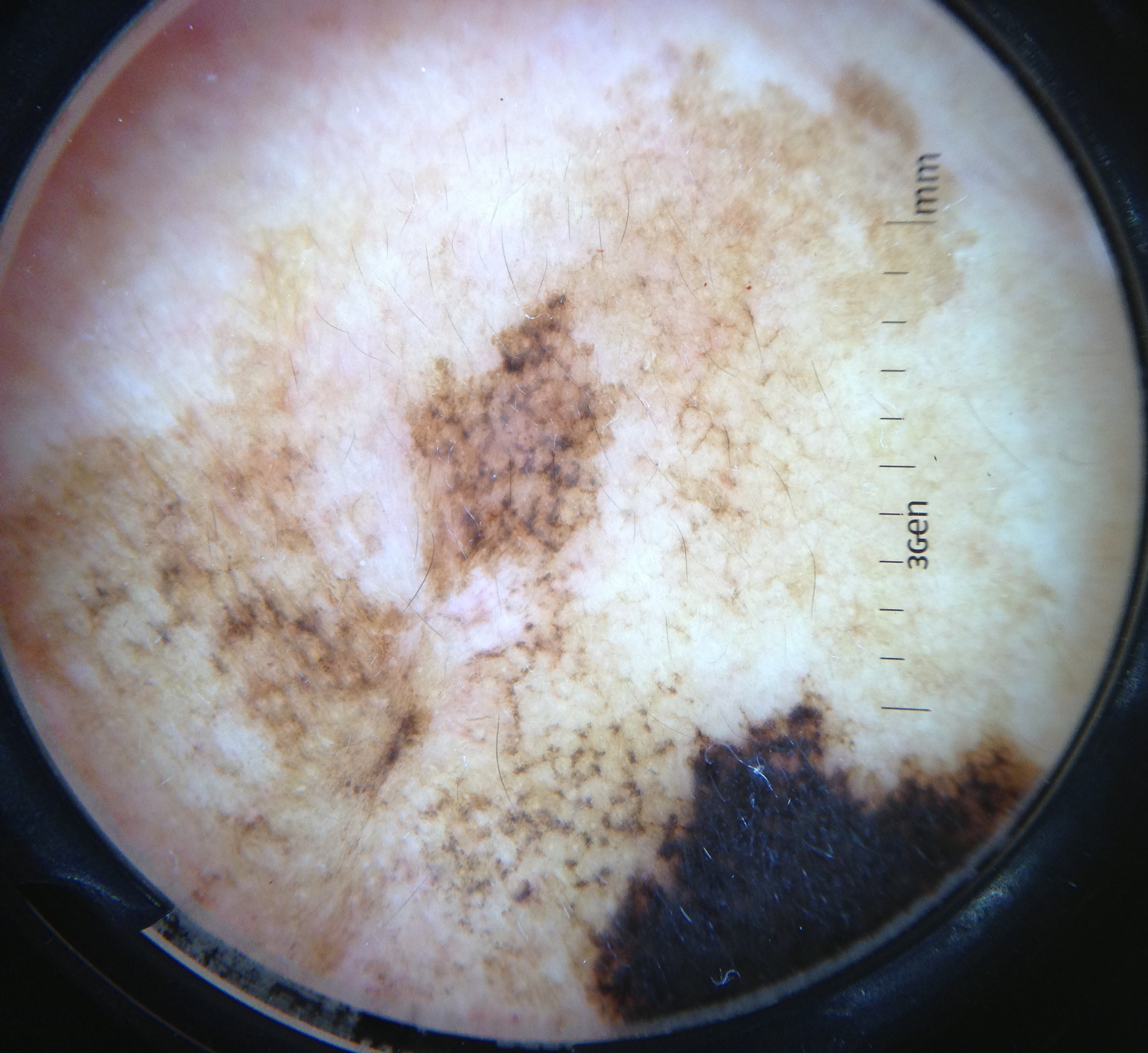Histopathology confirmed a lentigo maligna.